A dermoscopy image of a single skin lesion · a male subject approximately 60 years of age:
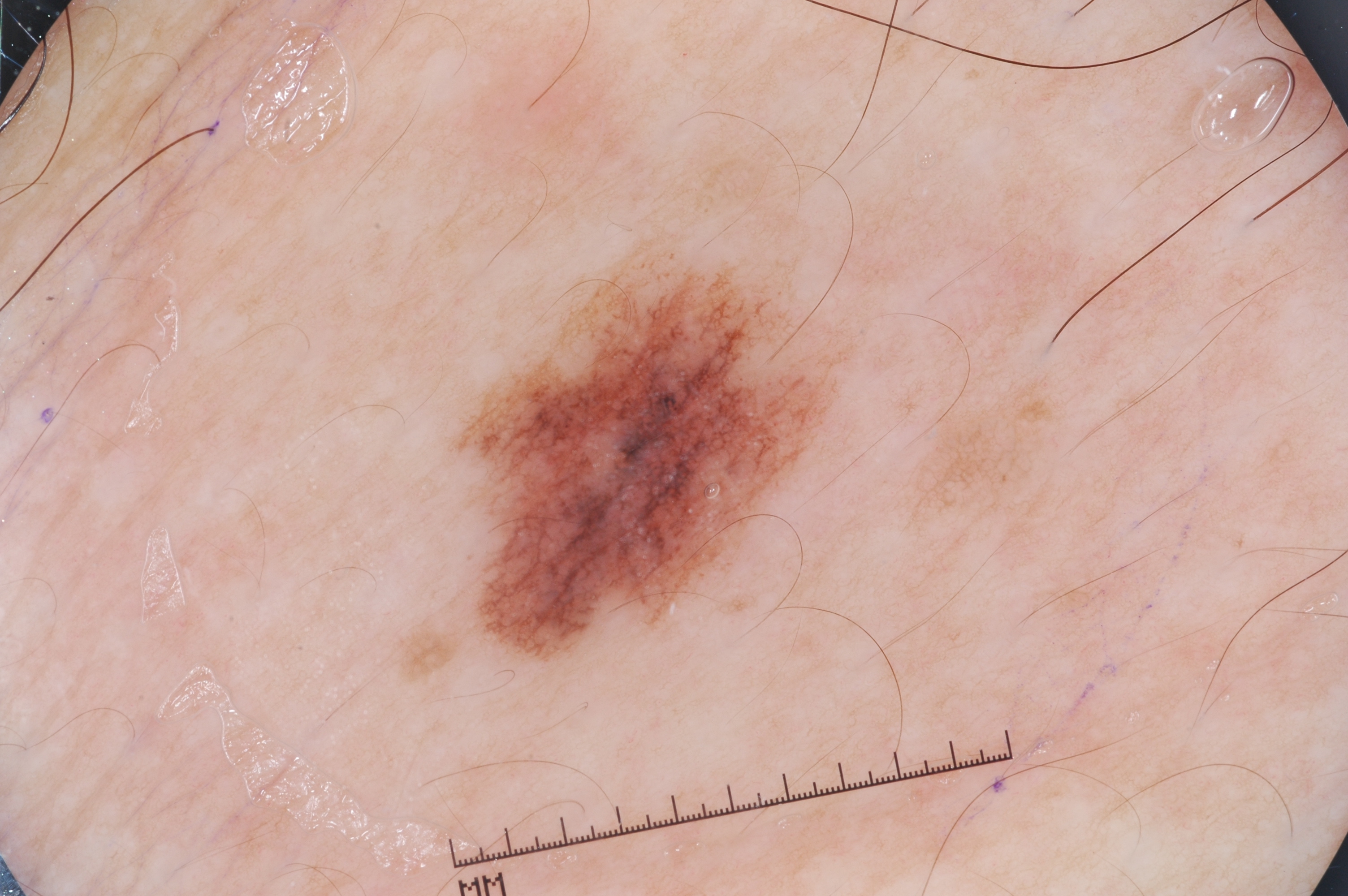Q: Where is the lesion located?
A: 474 273 822 651
Q: Which dermoscopic features were noted?
A: milia-like cysts and pigment network; absent: negative network and streaks
Q: What did the assessment conclude?
A: a melanocytic nevus, a benign skin lesion